An image taken at an angle — 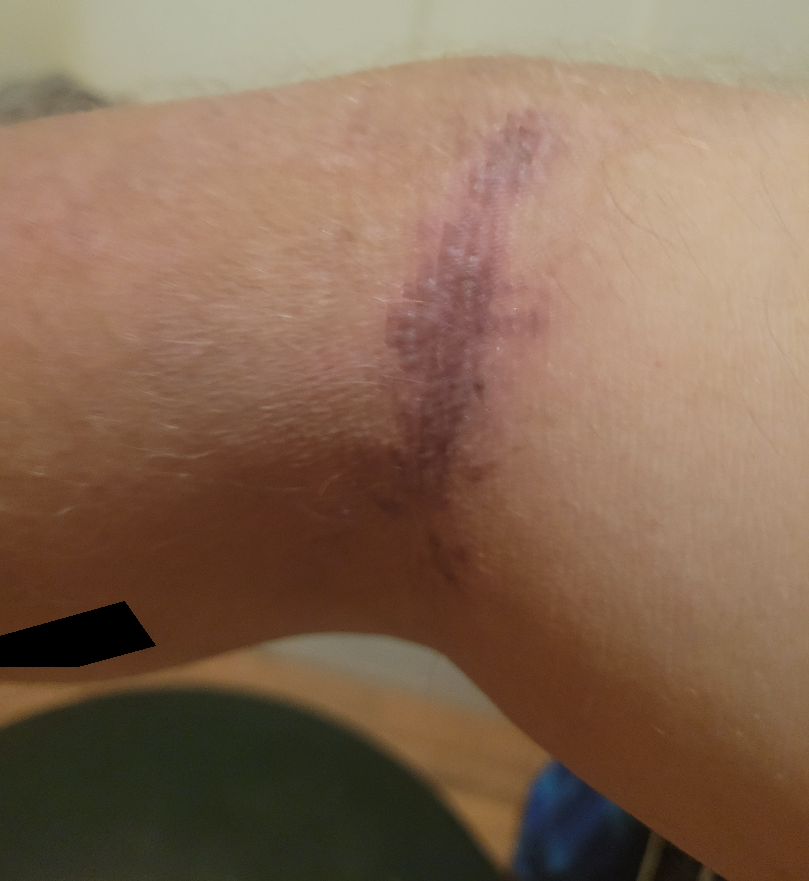clinical impression: ecchymoses (most likely).